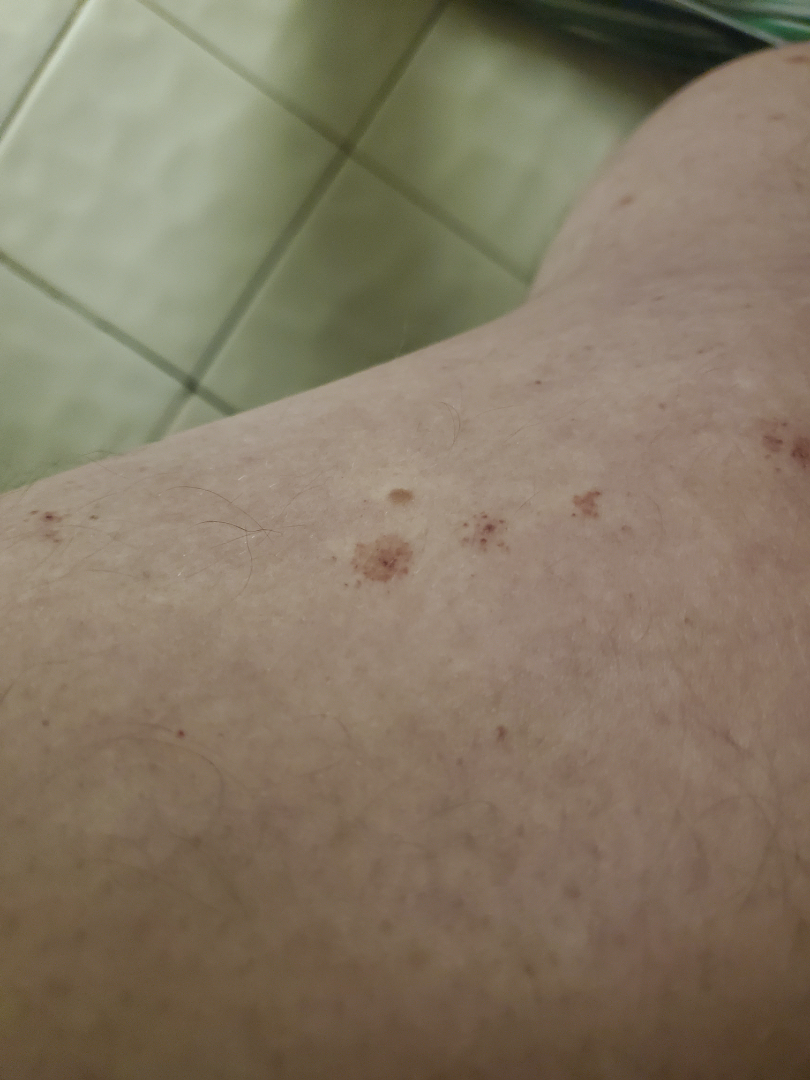Impression: The image was not sufficient for the reviewer to characterize the skin condition. History: Texture is reported as flat. Reported duration is one to four weeks. Reported lesion symptoms include bothersome appearance. The lesion involves the leg. The photo was captured at an angle. Self-categorized by the patient as skin that appeared healthy to them. Skin tone: Fitzpatrick III; lay reviewers estimated Monk skin tone scale 2.